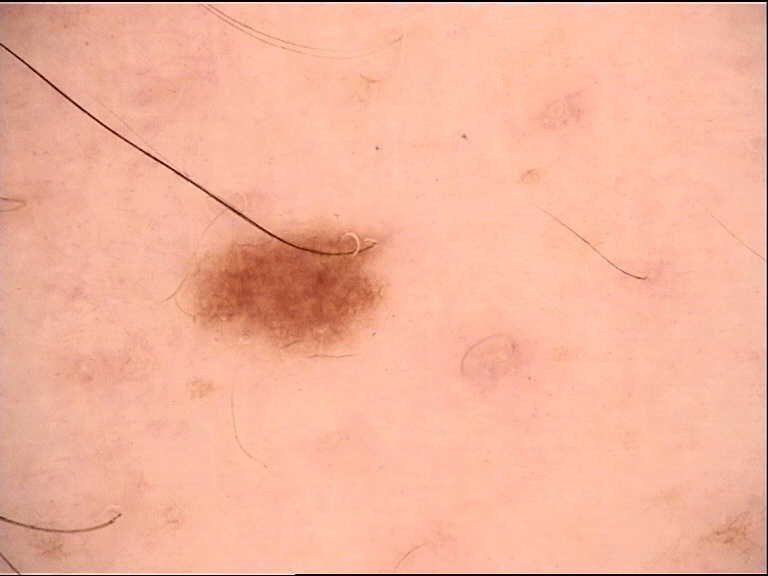image=dermoscopy; diagnosis=dysplastic junctional nevus (expert consensus).